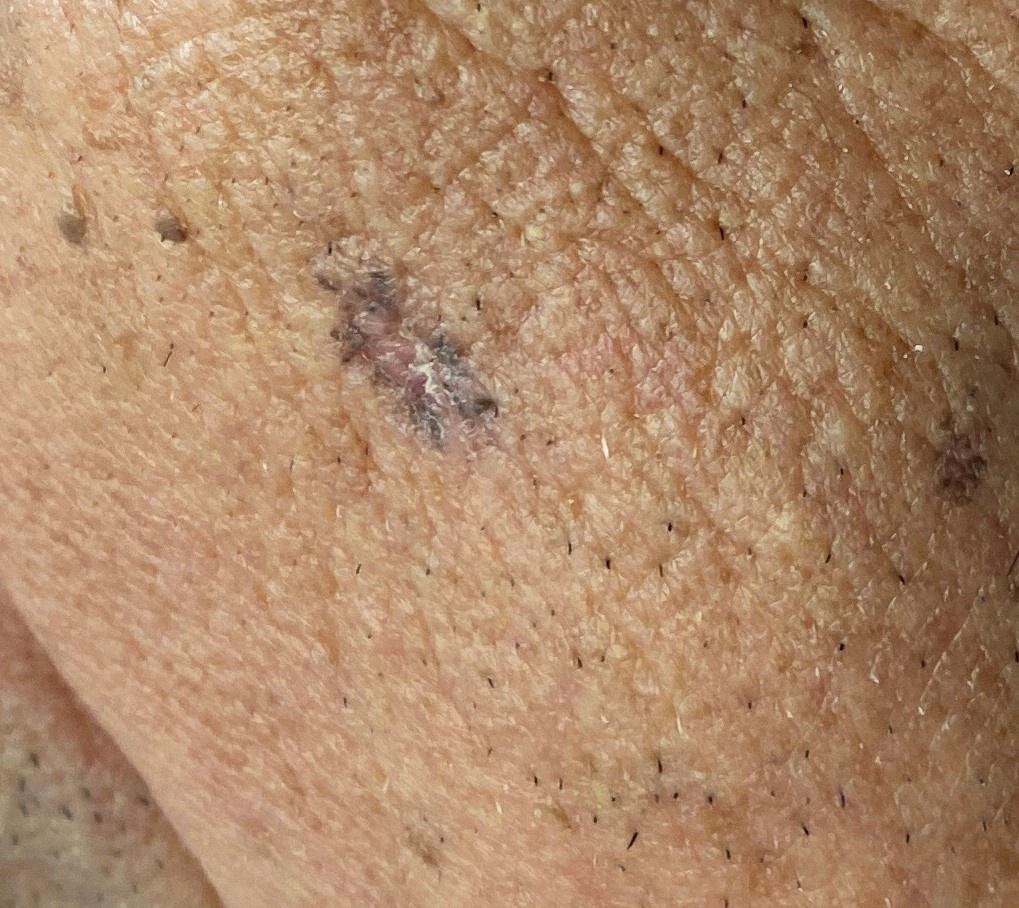The patient is FST III. A male subject aged approximately 85 or older. A clinical overview photograph of a skin lesion. The lesion is on the head or neck. On biopsy, the diagnosis was a malignant, adnexal lesion — a basal cell carcinoma.